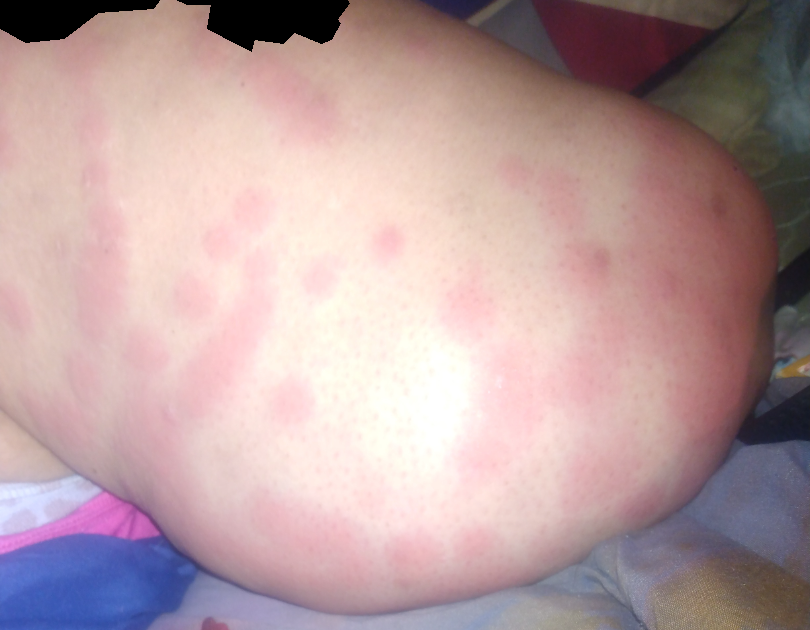The lesion is described as raised or bumpy.
Symptoms reported: enlargement, itching and burning.
The photograph is a close-up of the affected area.
The contributor is 40–49, female.
Present for less than one week.
The patient considered this a rash.
Fitzpatrick IV; lay reviewers estimated a Monk skin tone scale of 3.
The lesion involves the arm, palm and head or neck.
Reviewed remotely by three dermatologists: the favored diagnosis is Urticaria; also consider Leukocytoclastic Vasculitis; less probable is Insect Bite.